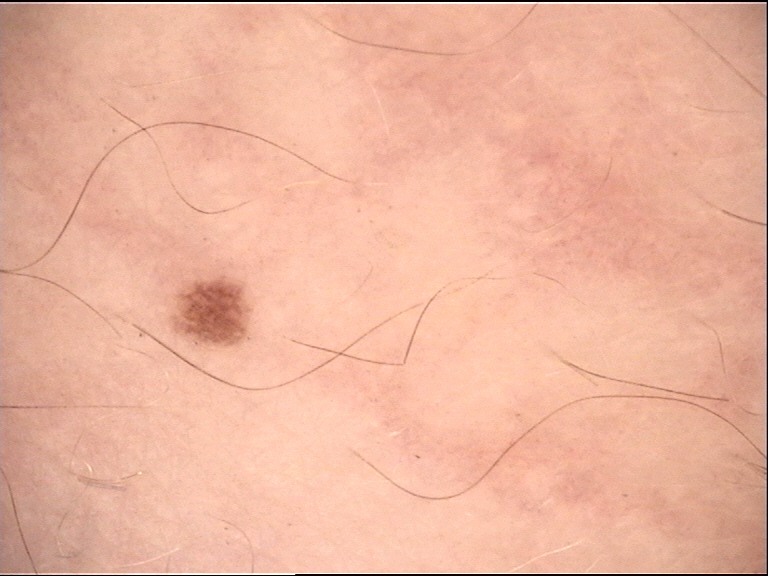A dermoscopic close-up of a skin lesion.
Diagnosed as a banal lesion — a junctional nevus.